The photograph was taken at a distance · located on the leg:
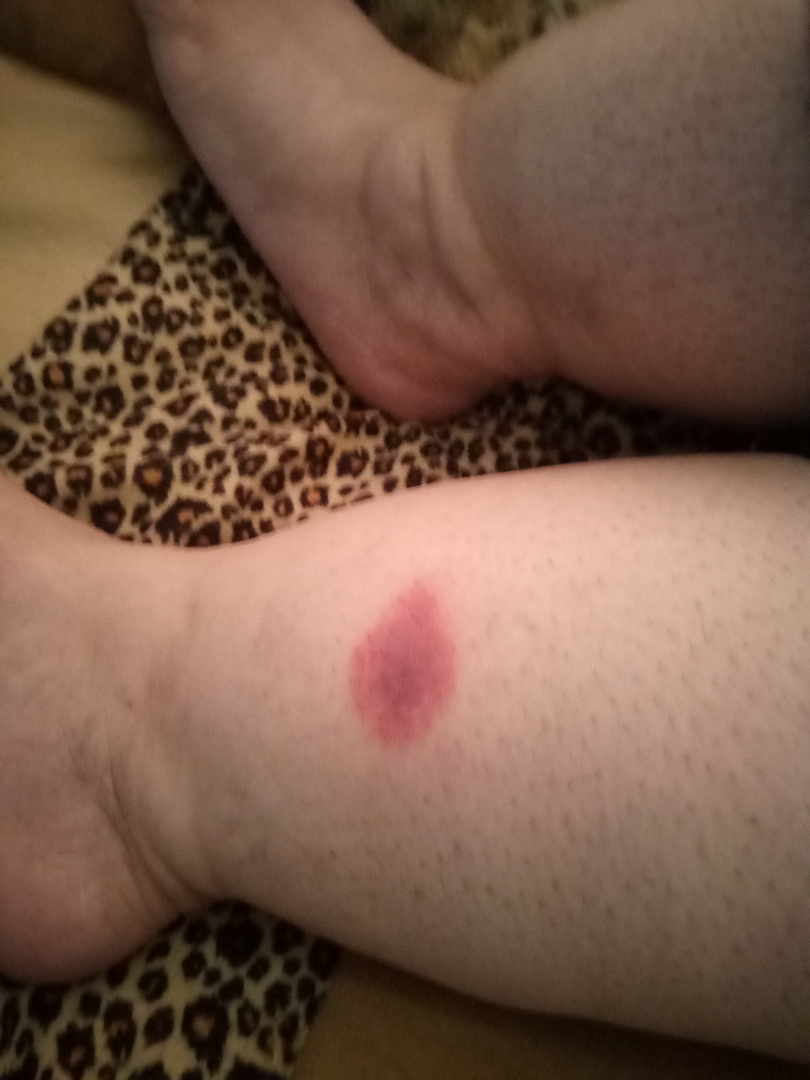surface texture: rough or flaky | skin tone: human graders estimated 2 on the Monk skin tone scale | history: less than one week | diagnostic considerations: Insect Bite (weight 0.67); ecchymoses (weight 0.33).